An image taken at an angle. The lesion involves the leg.
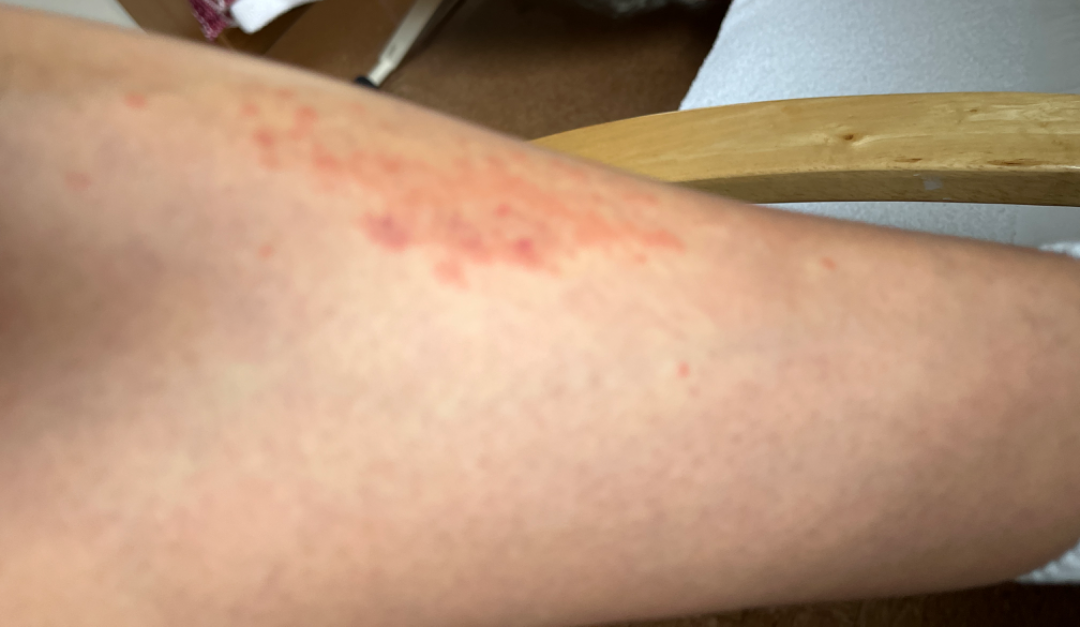Notes:
– assessment · indeterminate from the photograph
– lesion texture · raised or bumpy
– skin tone · Fitzpatrick skin type IV; lay reviewers estimated MST 1 or 2 (two reviewer pools)
– onset · less than one week